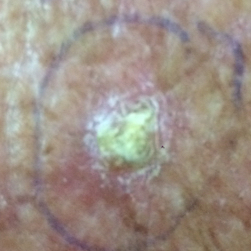Q: What is the patient's skin type?
A: II
Q: What does the exposure history note?
A: pesticide exposure, no prior malignancy (patient or family), no tobacco use
Q: Who is the patient?
A: female, aged 56
Q: What is the imaging modality?
A: smartphone clinical photo
Q: Where on the body is the lesion?
A: the chest
Q: What are the lesion's dimensions?
A: approx. 9 × 6 mm
Q: Any reported symptoms?
A: itching, growth, elevation
Q: What is this lesion?
A: basal cell carcinoma (biopsy-proven)